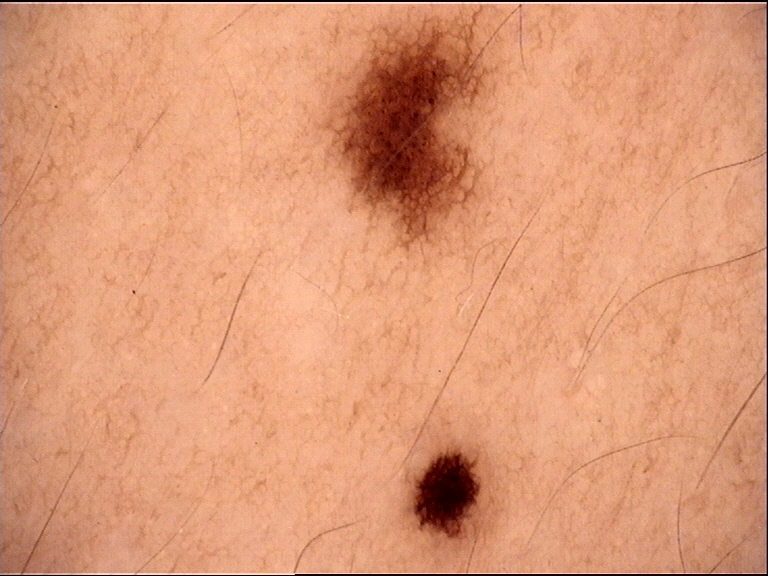Case: A dermoscopic photograph of a skin lesion. Conclusion: The diagnostic label was a dysplastic junctional nevus.